A male patient in their 50s; by history, prior skin cancer (patient or family).
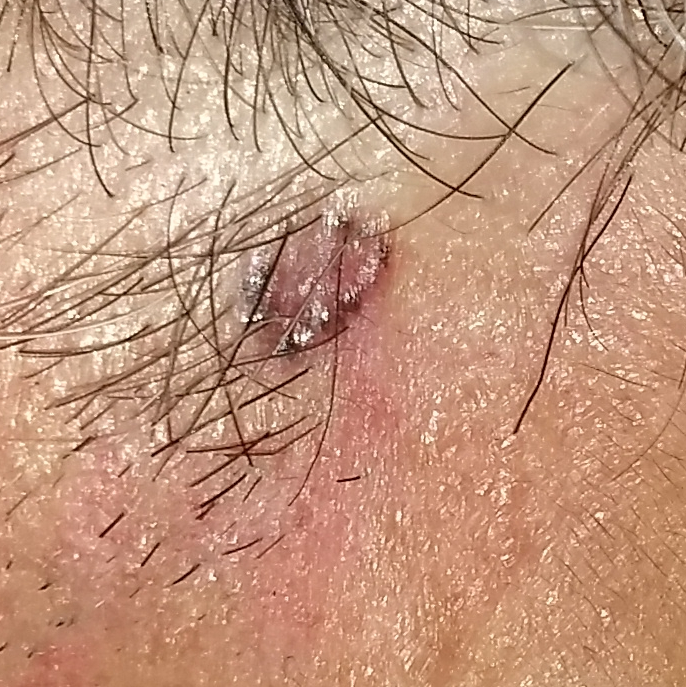Clinical context: The lesion involves an ear. The lesion measures approximately 7 × 5 mm. The patient describes that the lesion is elevated and has bled, but has not grown and does not hurt. Conclusion: Confirmed on histopathology as a basal cell carcinoma.